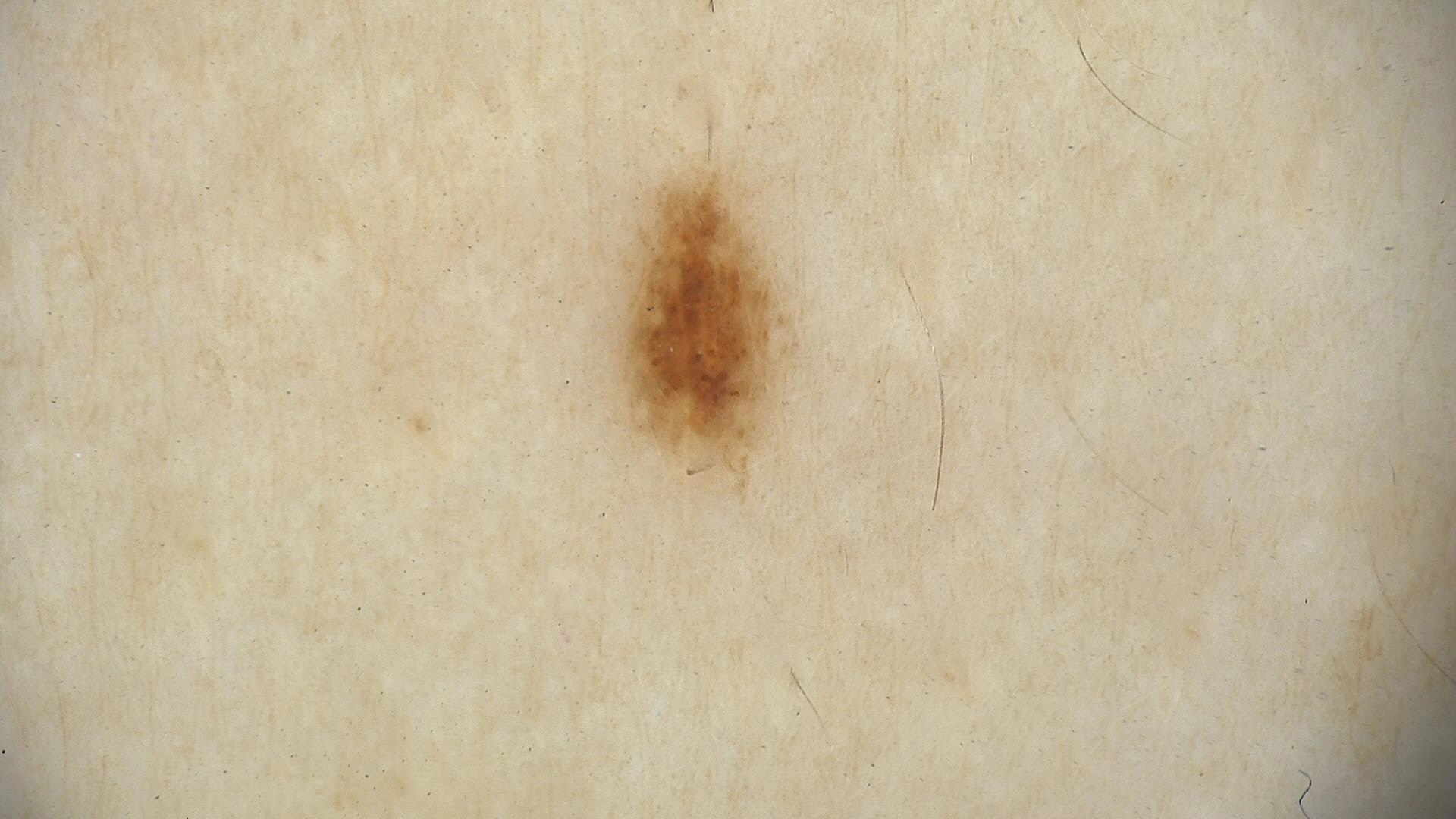Findings:
• image type · dermatoscopy
• assessment · dysplastic junctional nevus (expert consensus)